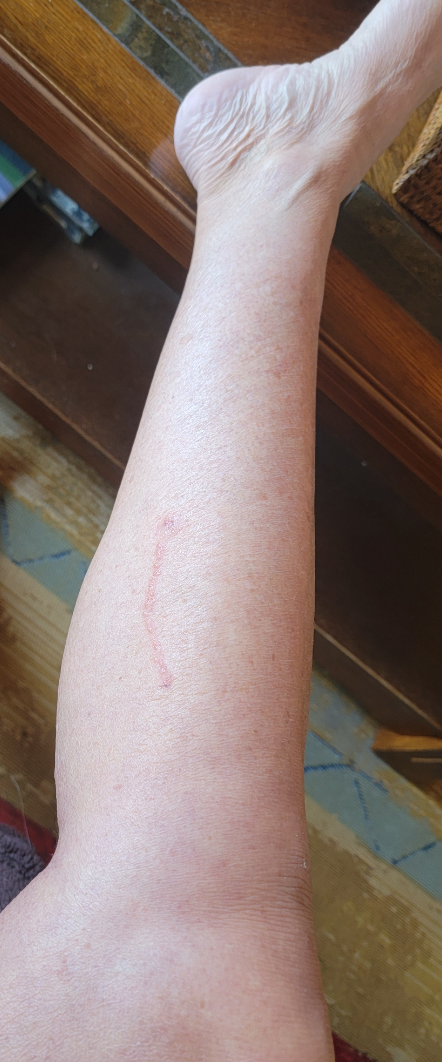Lichen striatus (54%); Herpes Zoster (23%); Allergic Contact Dermatitis (23%).